A dermatoscopic image of a skin lesion.
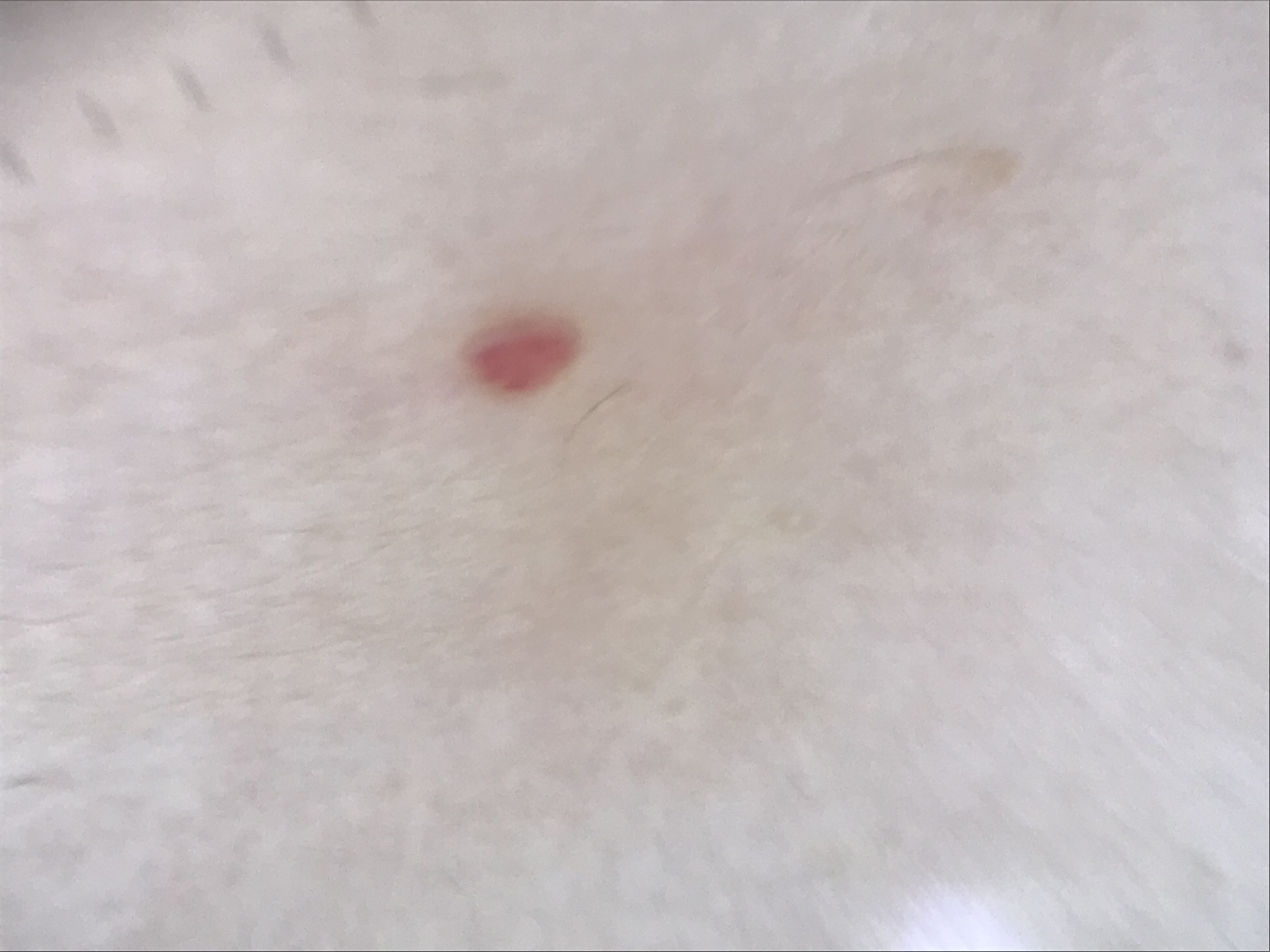Findings:
• diagnosis: hemangioma (expert consensus)